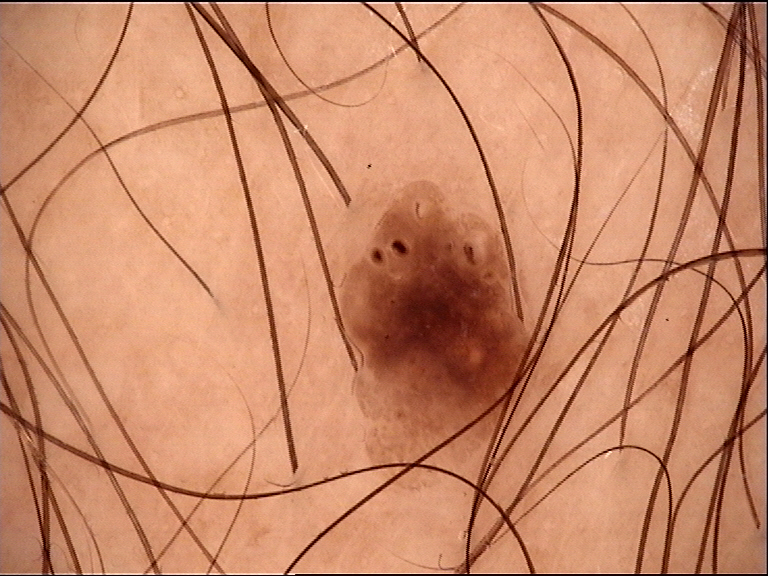Labeled as a seborrheic keratosis.